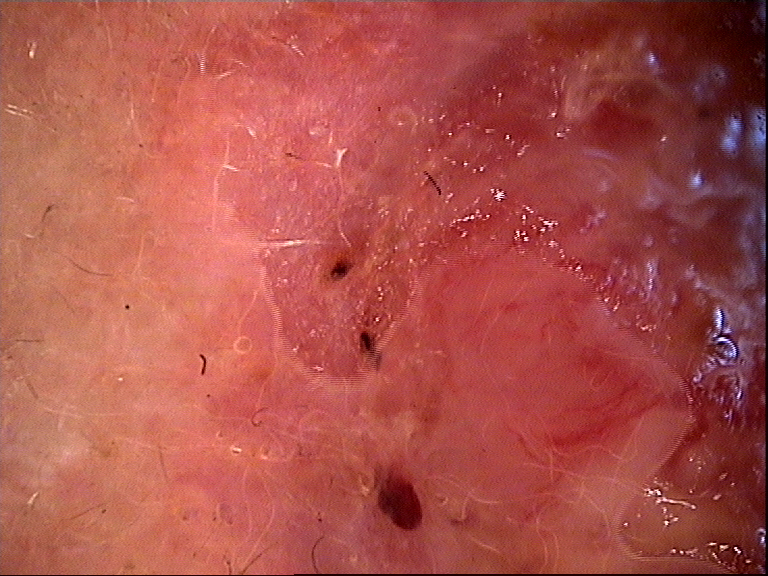Findings:
• image — dermatoscopy
• class — basal cell carcinoma (biopsy-proven)